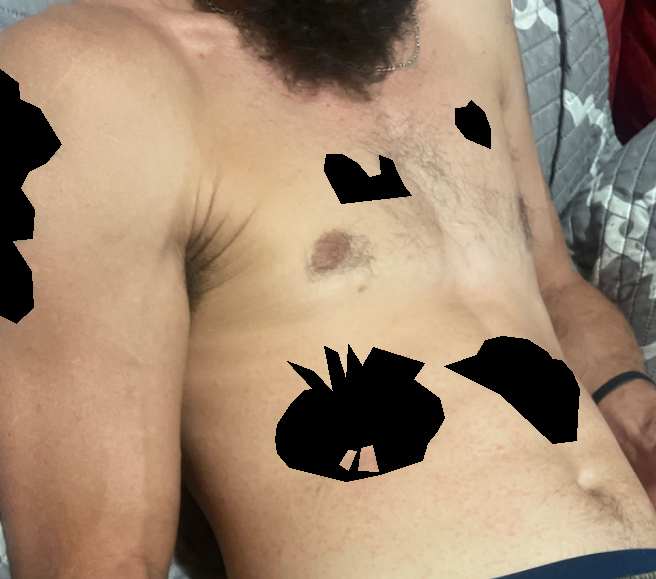The patient considered this a rash.
The patient indicates the lesion is raised or bumpy.
Fitzpatrick phototype II.
An image taken at a distance.
Present for about one day.
Located on the front of the torso.
Symptoms reported: bothersome appearance and enlargement.
A single dermatologist reviewed the case: Drug Rash and Viral Exanthem were each considered, in no particular order; a more distant consideration is Miliaria.